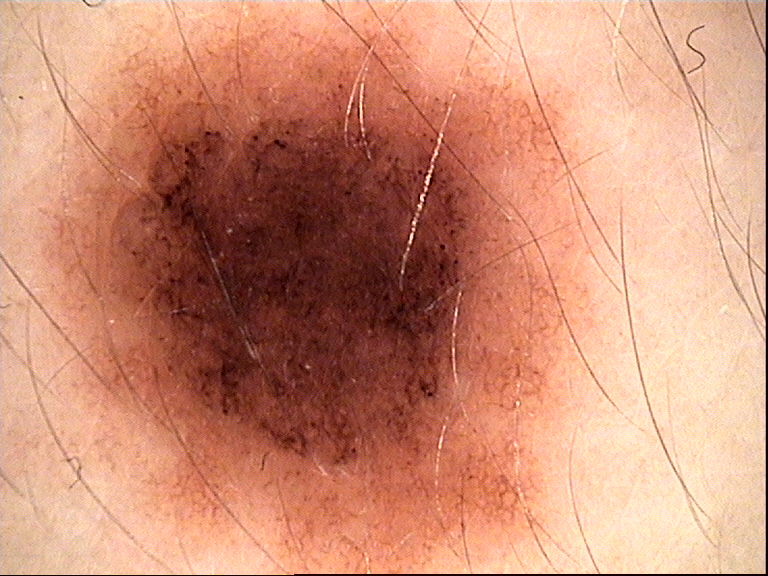Diagnosed as a dysplastic compound nevus.